A close-up photograph.
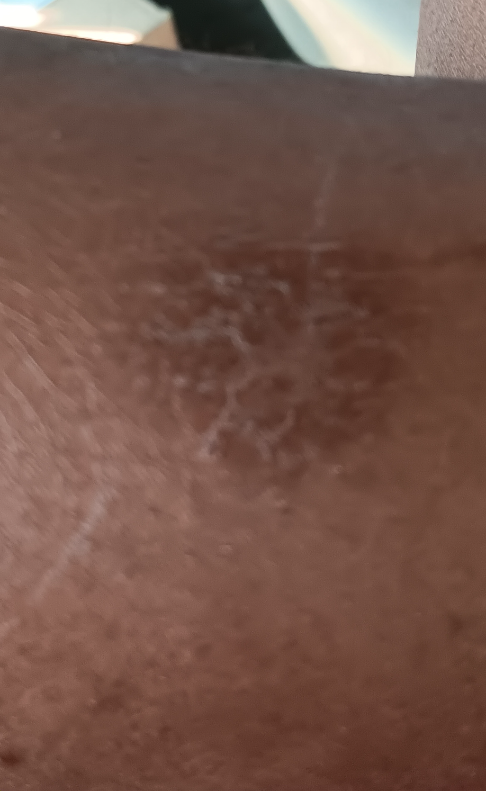Notes:
– assessment — indeterminate